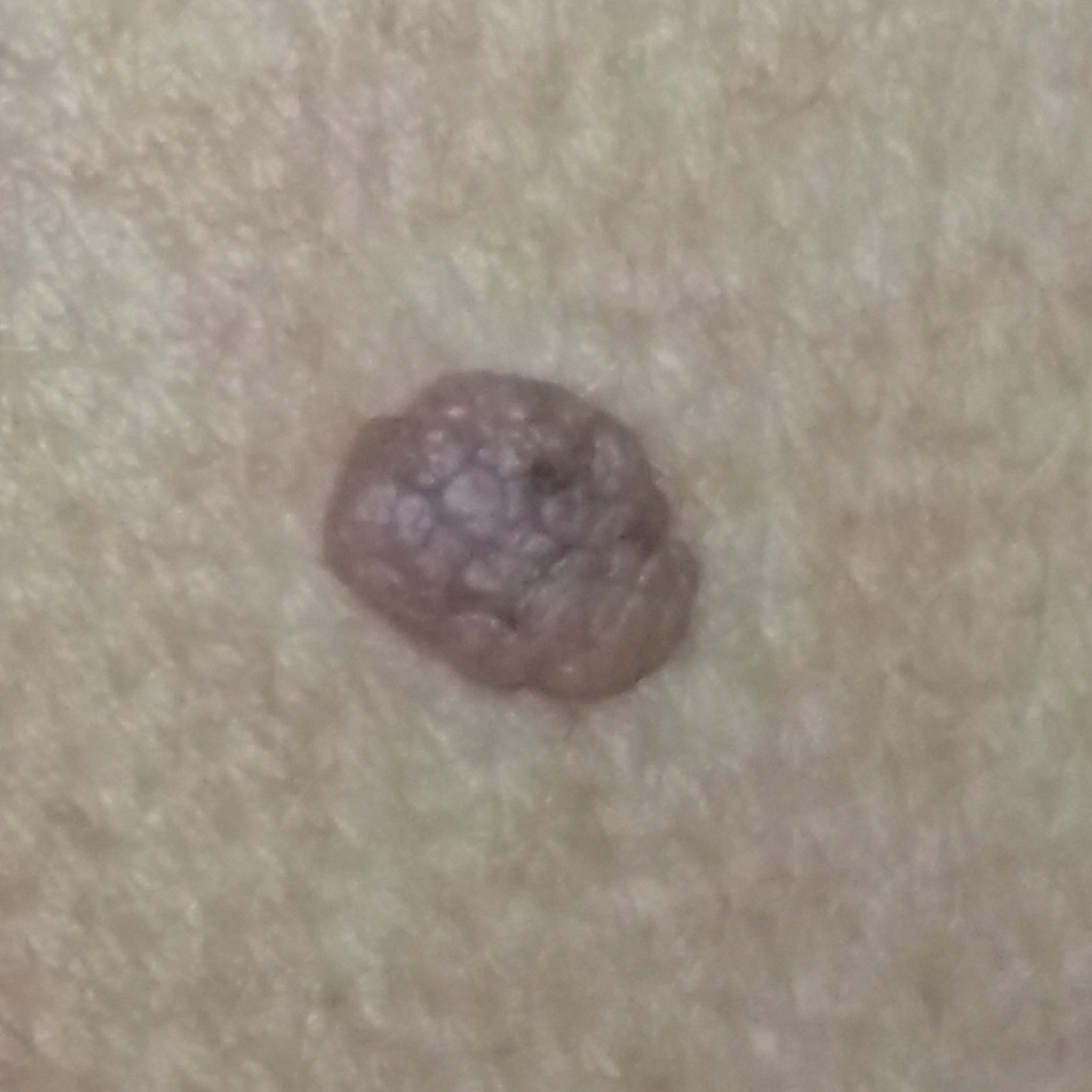A smartphone photograph of a skin lesion.
The lesion was found on the back.
The patient describes that the lesion is elevated and has grown.
Consistent with a nevus.